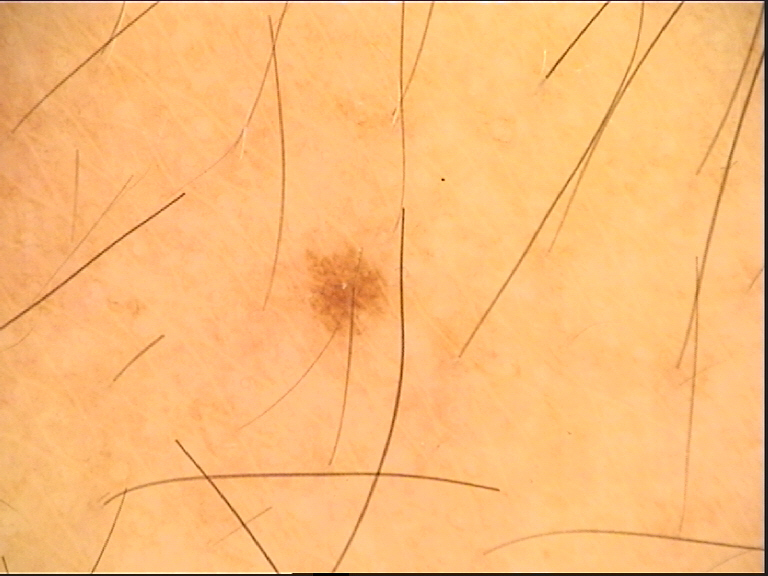label = dysplastic junctional nevus (expert consensus)